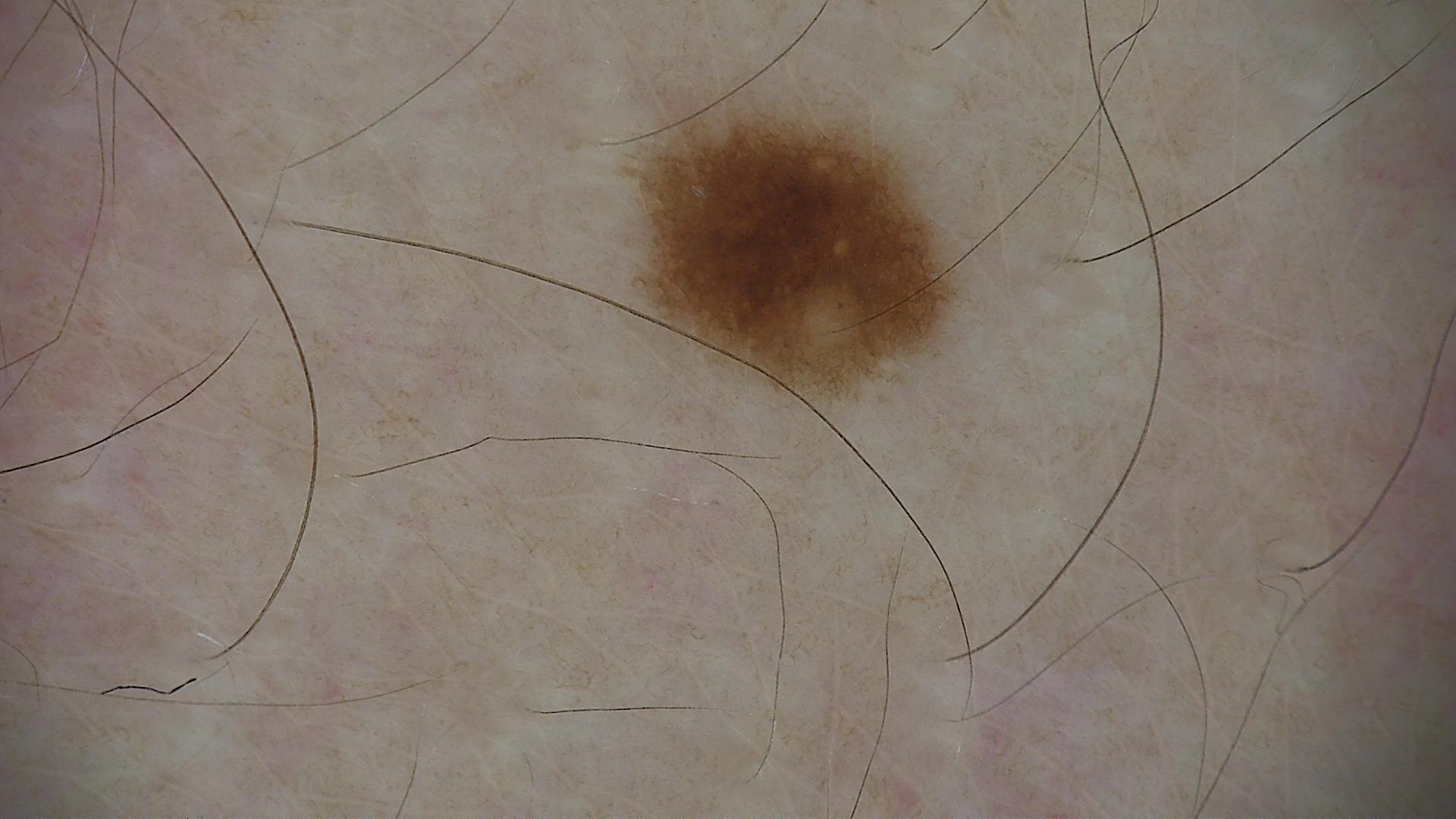imaging=dermoscopy
diagnosis=junctional nevus (expert consensus)